The subject is a female aged approximately 20; a dermoscopic image of a skin lesion.
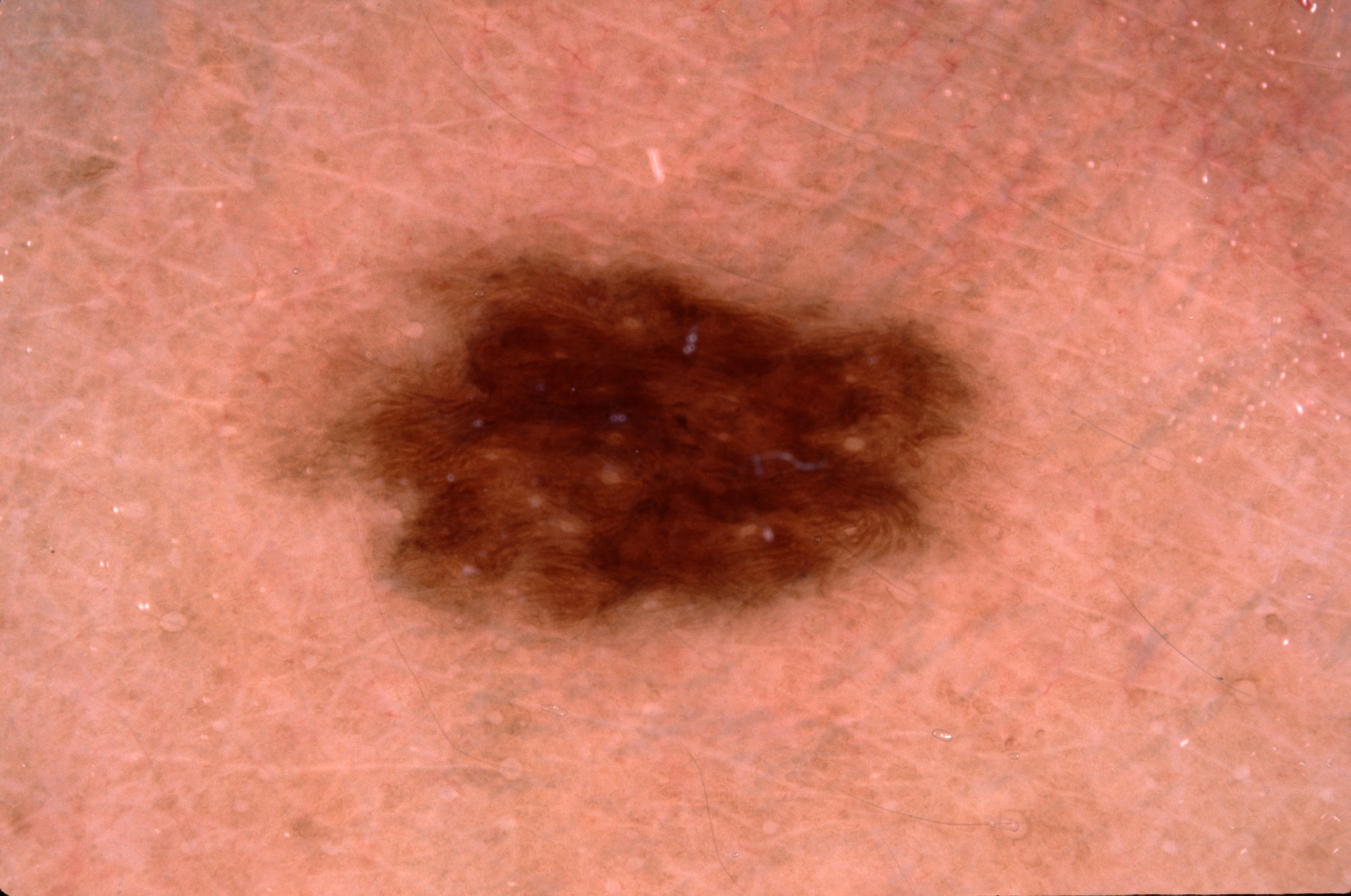The lesion occupies roughly 20% of the field. As (left, top, right, bottom), the visible lesion spans <bbox>260, 194, 1013, 662</bbox>. The dermoscopic pattern shows no pigment network, negative network, streaks, or milia-like cysts. The clinical diagnosis was a melanocytic nevus, a benign lesion.